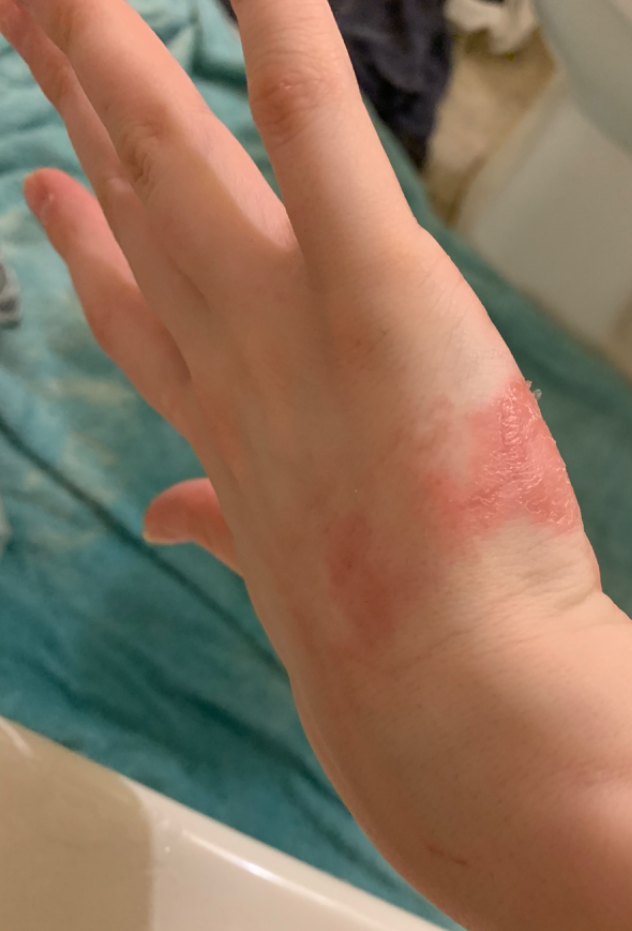Most consistent with Psoriasis; with consideration of Irritant Contact Dermatitis; less likely is Tinea; less probable is Eczema; a more distant consideration is Burn erythema of back of hand.